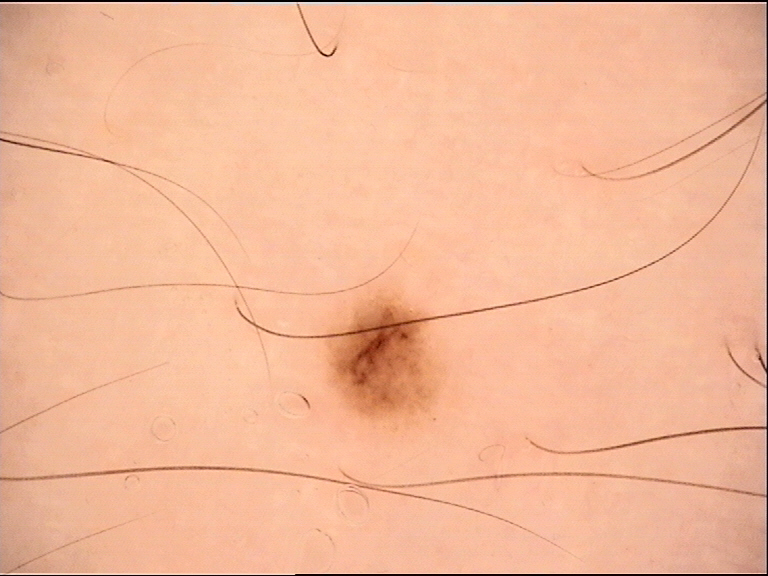{
  "image": "dermatoscopy",
  "diagnosis": {
    "name": "dysplastic junctional nevus",
    "code": "jd",
    "malignancy": "benign",
    "super_class": "melanocytic",
    "confirmation": "expert consensus"
  }
}